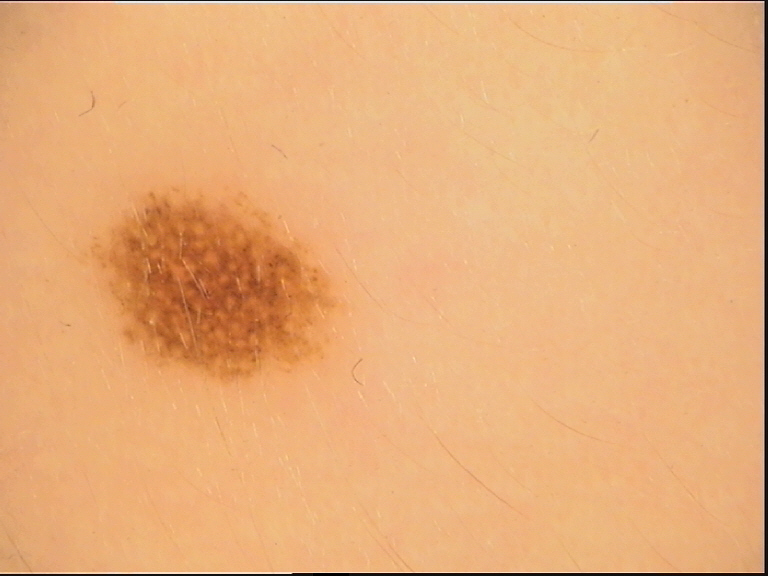image type: dermatoscopy; class: dysplastic compound nevus (expert consensus).